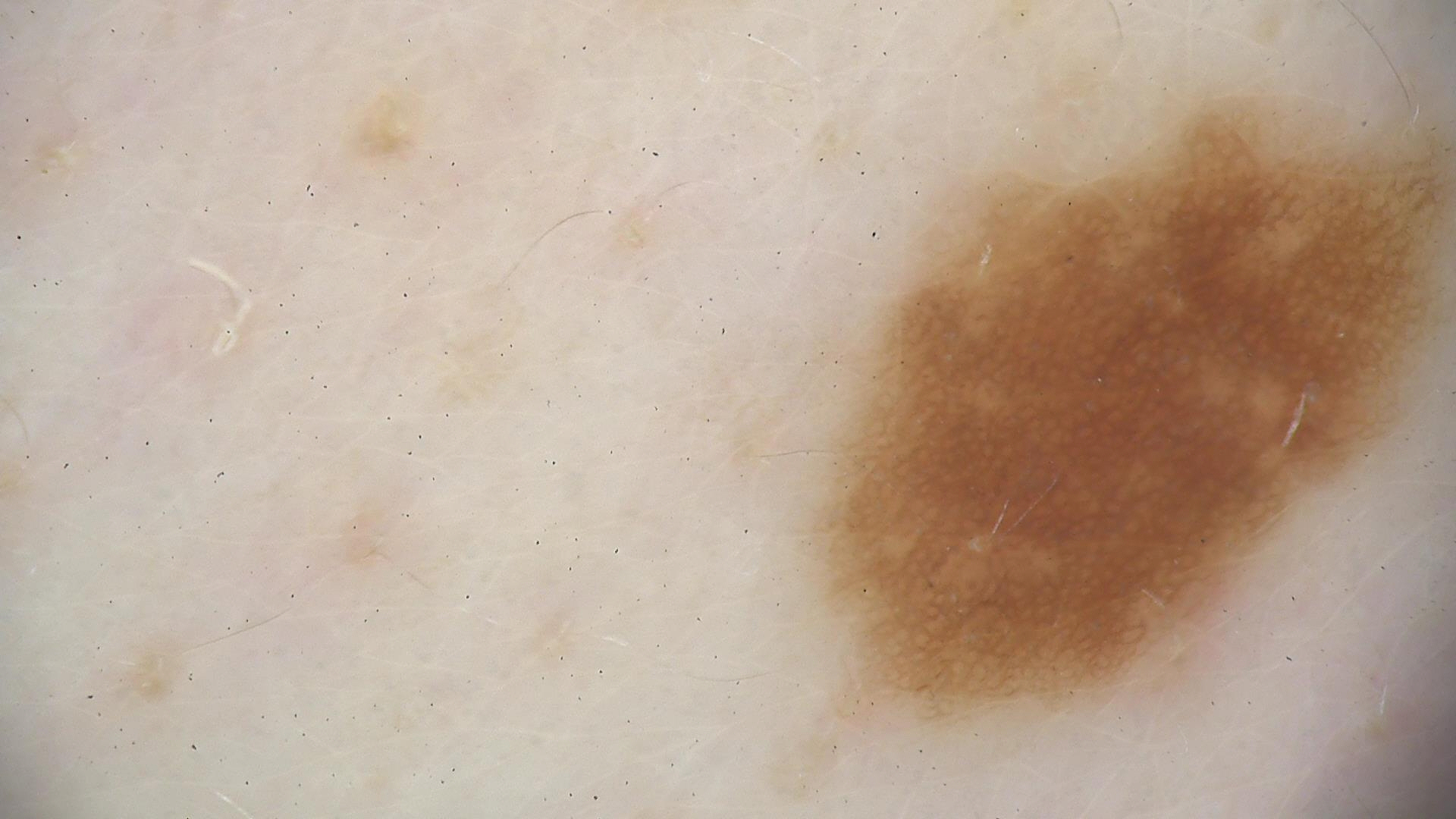Summary: A skin lesion imaged with a dermatoscope. Conclusion: The diagnostic label was a dysplastic junctional nevus.